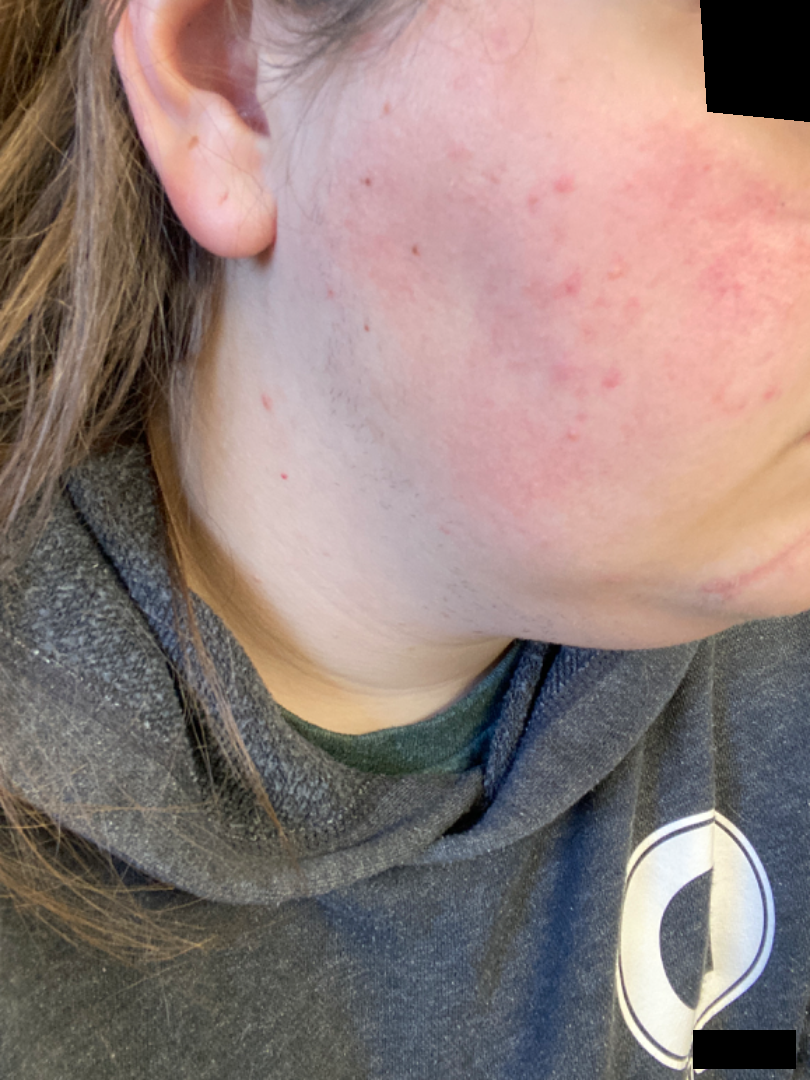reported symptoms = none reported
framing = at an angle
described texture = raised or bumpy
subject = female, age 18–29
patient's own categorization = a rash
differential diagnosis = the impression on review was Rosacea